The lesion involves the arm, this image was taken at a distance.
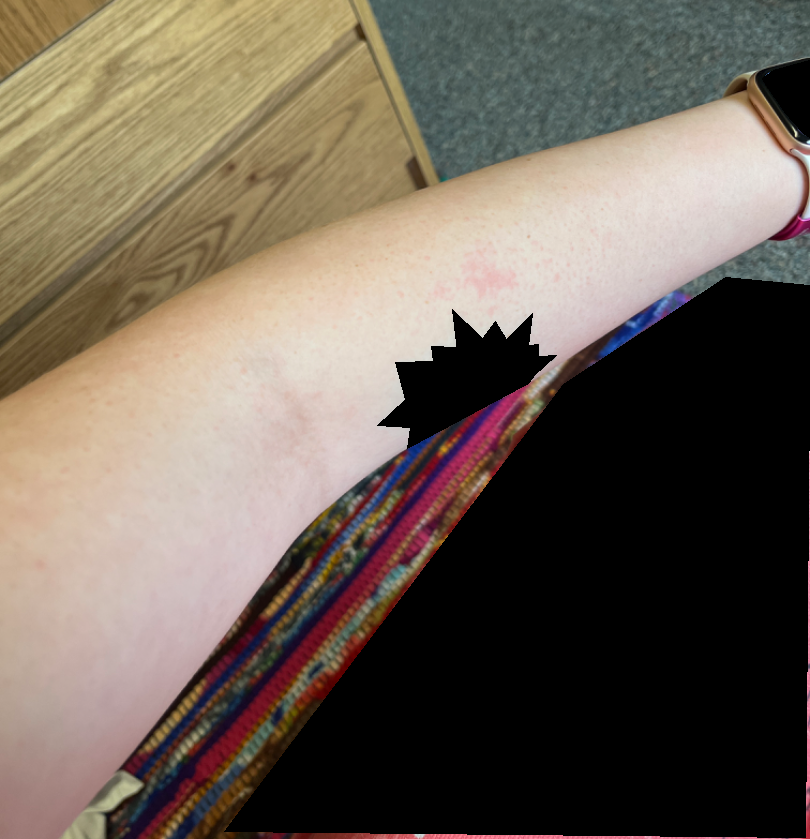The skin condition could not be confidently assessed from this image.